The photograph was taken at a distance. Male patient, age 18–29. The lesion involves the front of the torso, back of the hand, leg, top or side of the foot, back of the torso and arm — 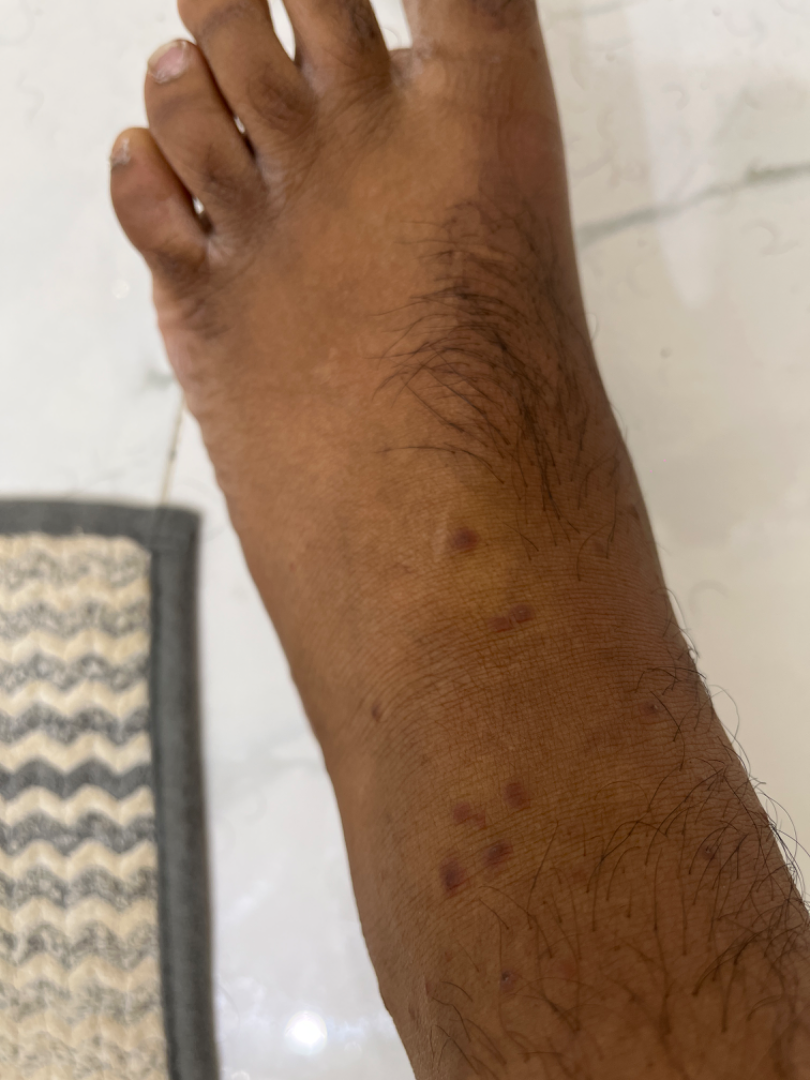dermatologist impression: the favored diagnosis is Folliculitis; lower on the differential is Psoriasis; less probable is Perifolliculitis